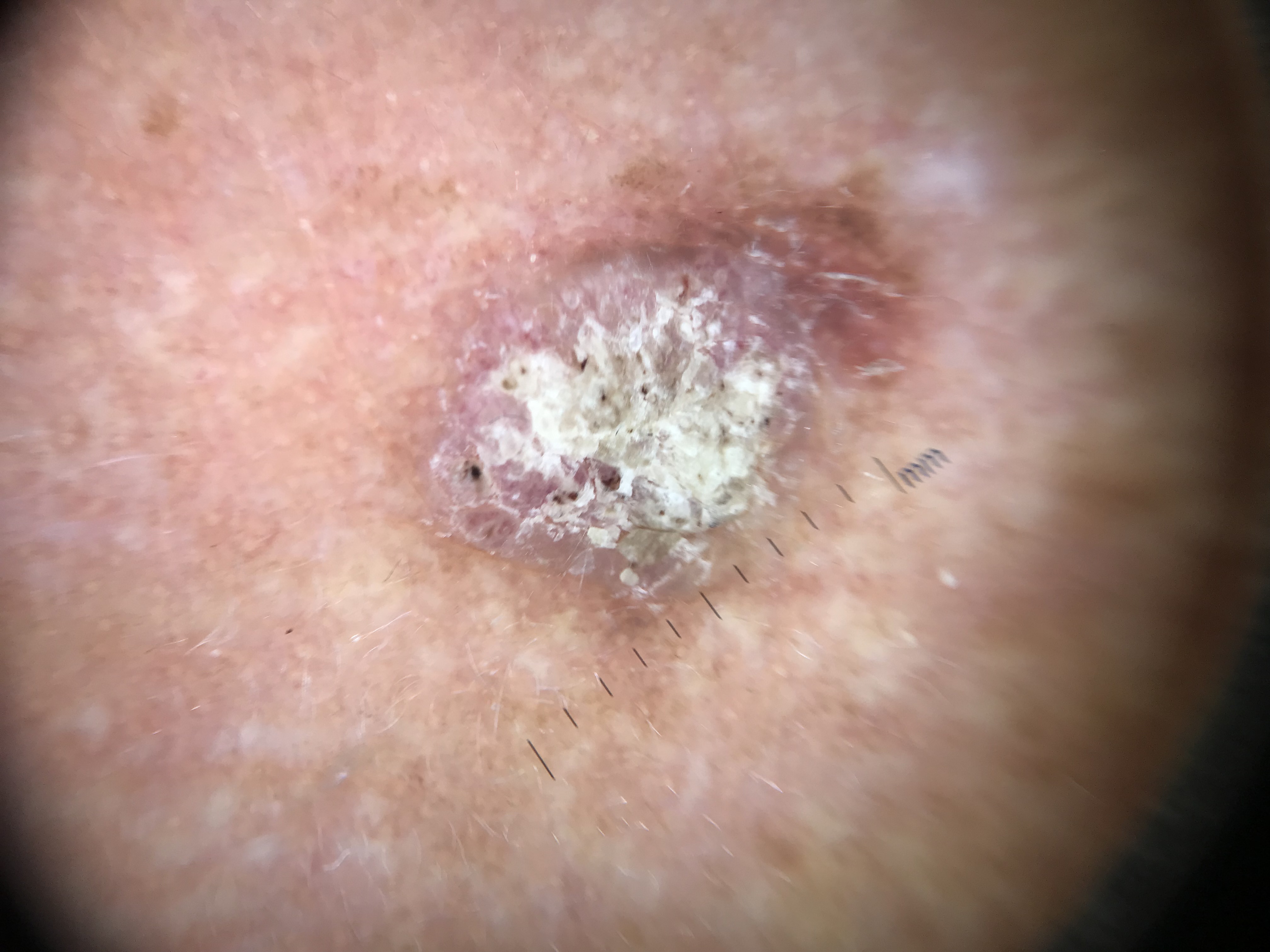<lesion>
<image>dermatoscopy</image>
<lesion_type>
<main_class>keratinocytic</main_class>
</lesion_type>
<diagnosis>
<name>squamous cell carcinoma</name>
<code>scc</code>
<malignancy>malignant</malignancy>
<super_class>non-melanocytic</super_class>
<confirmation>histopathology</confirmation>
</diagnosis>
</lesion>